A dermoscopic close-up of a skin lesion. A male patient, aged approximately 75:
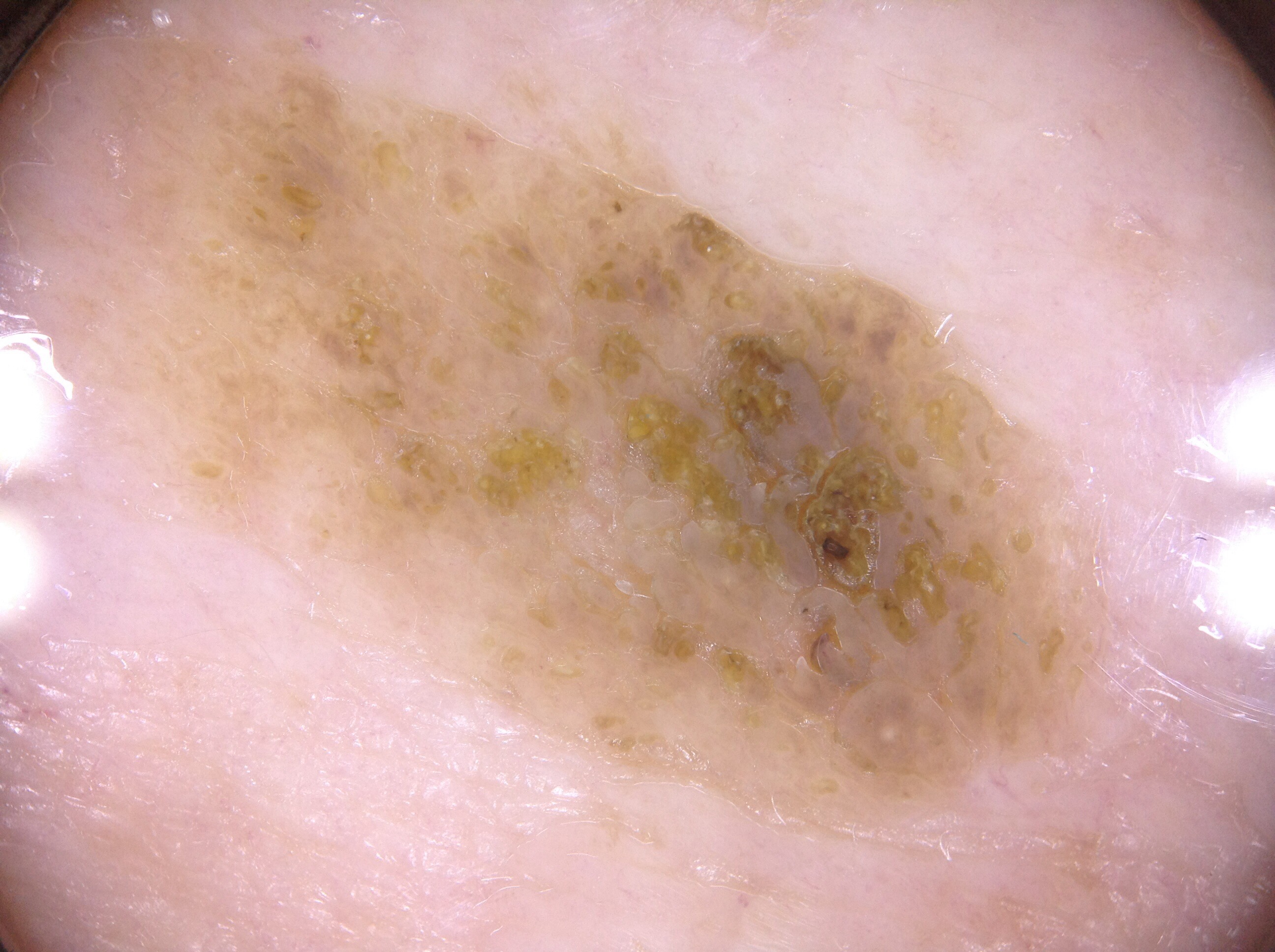As (left, top, right, bottom), the lesion is bounded by 90 82 1106 825. A prominent lesion filling much of the field. The dermoscopic pattern shows milia-like cysts; no pigment network, streaks, or negative network. The diagnostic assessment was a seborrheic keratosis.